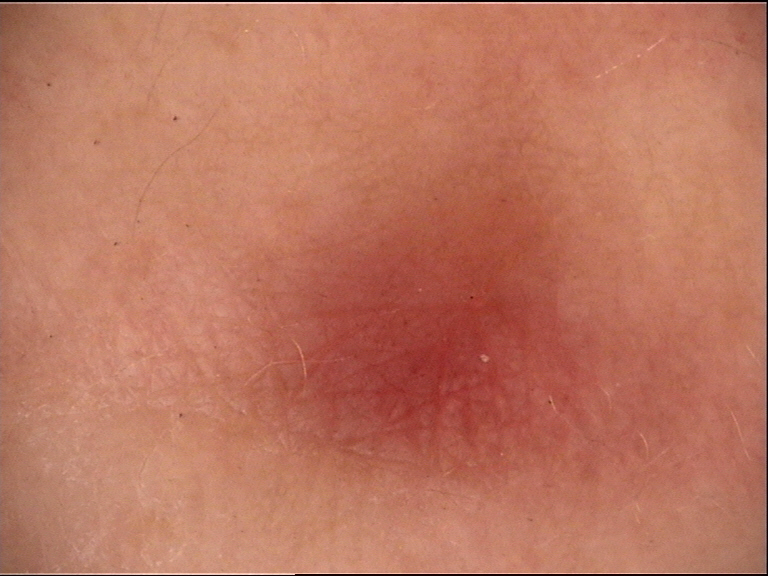Diagnosed as a dermatofibroma.